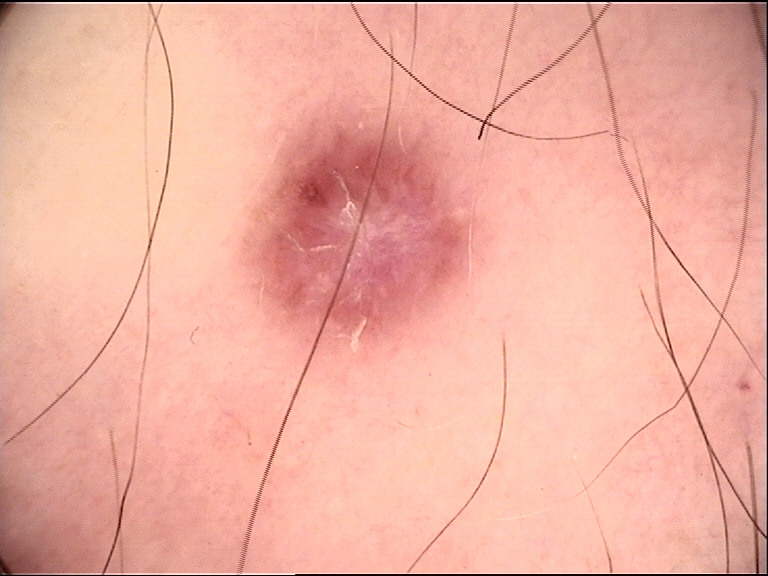Summary:
A dermoscopic image of a skin lesion.
Impression:
The diagnostic label was a benign, fibro-histiocytic lesion — a dermatofibroma.